A dermatoscopic image of a skin lesion: 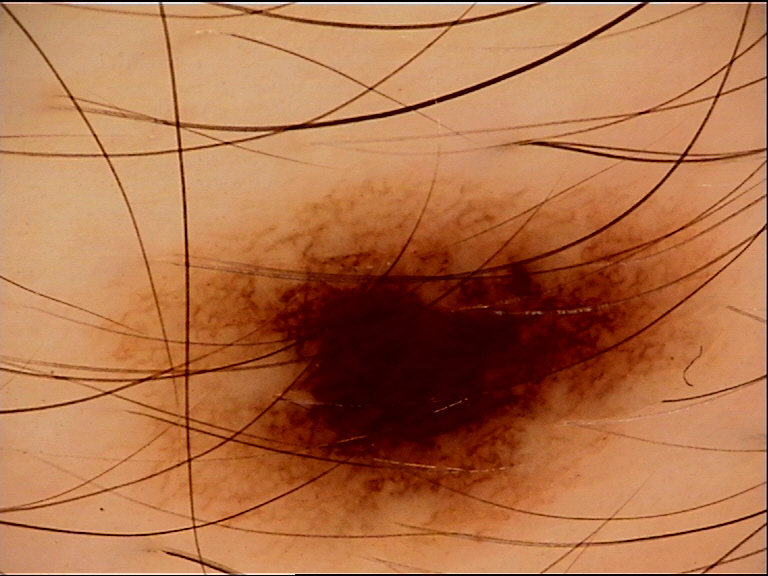assessment — dysplastic compound nevus (expert consensus)